Close-up view; the back of the torso, leg, head or neck, front of the torso and arm are involved; the patient is female.
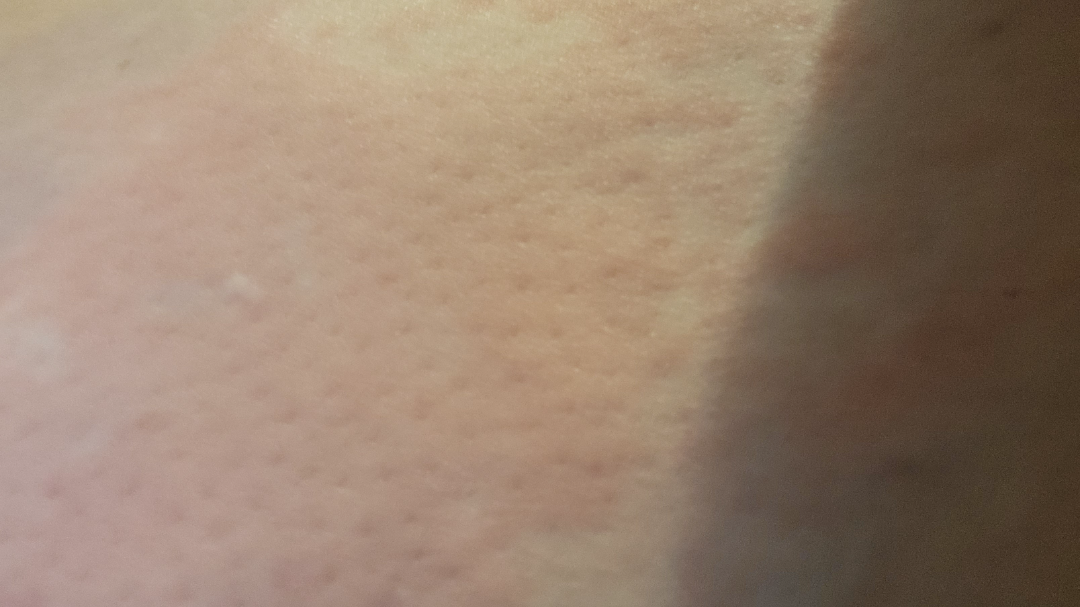<summary>
<assessment>ungradable on photographic review</assessment>
</summary>